A female patient, in their mid- to late 20s · a dermoscopic image of a skin lesion: 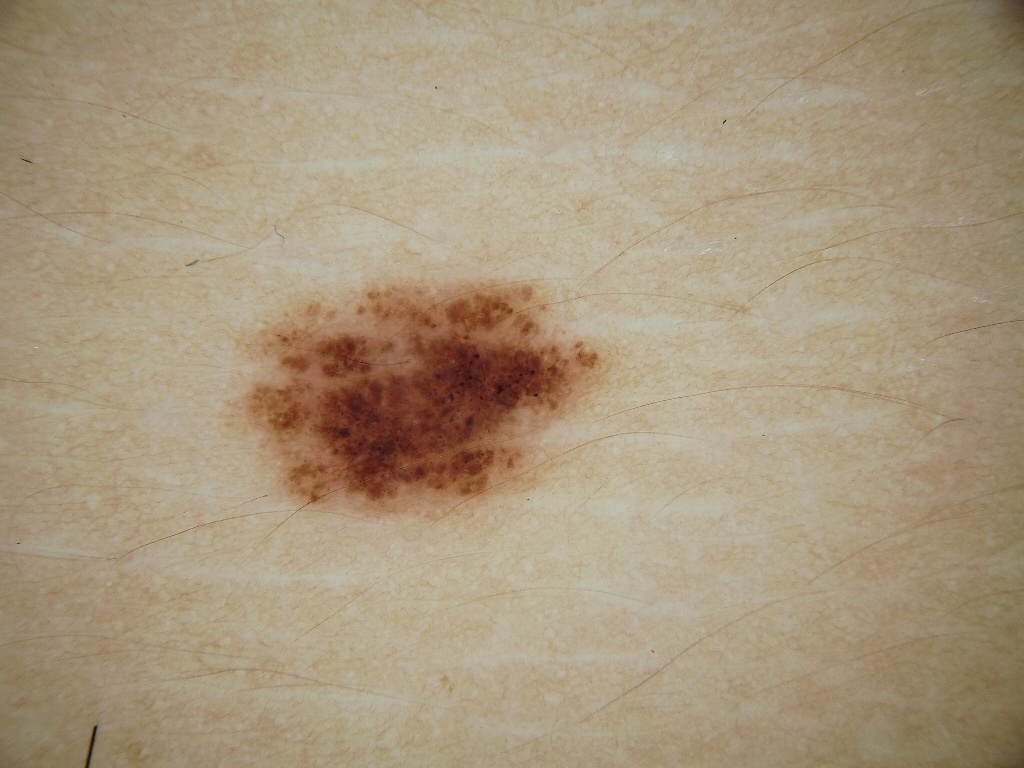Q: What dermoscopic features are present?
A: milia-like cysts, globules, and pigment network
Q: Where is the lesion located?
A: (236, 282, 601, 518)
Q: What did the assessment conclude?
A: a melanocytic nevus, a benign skin lesion